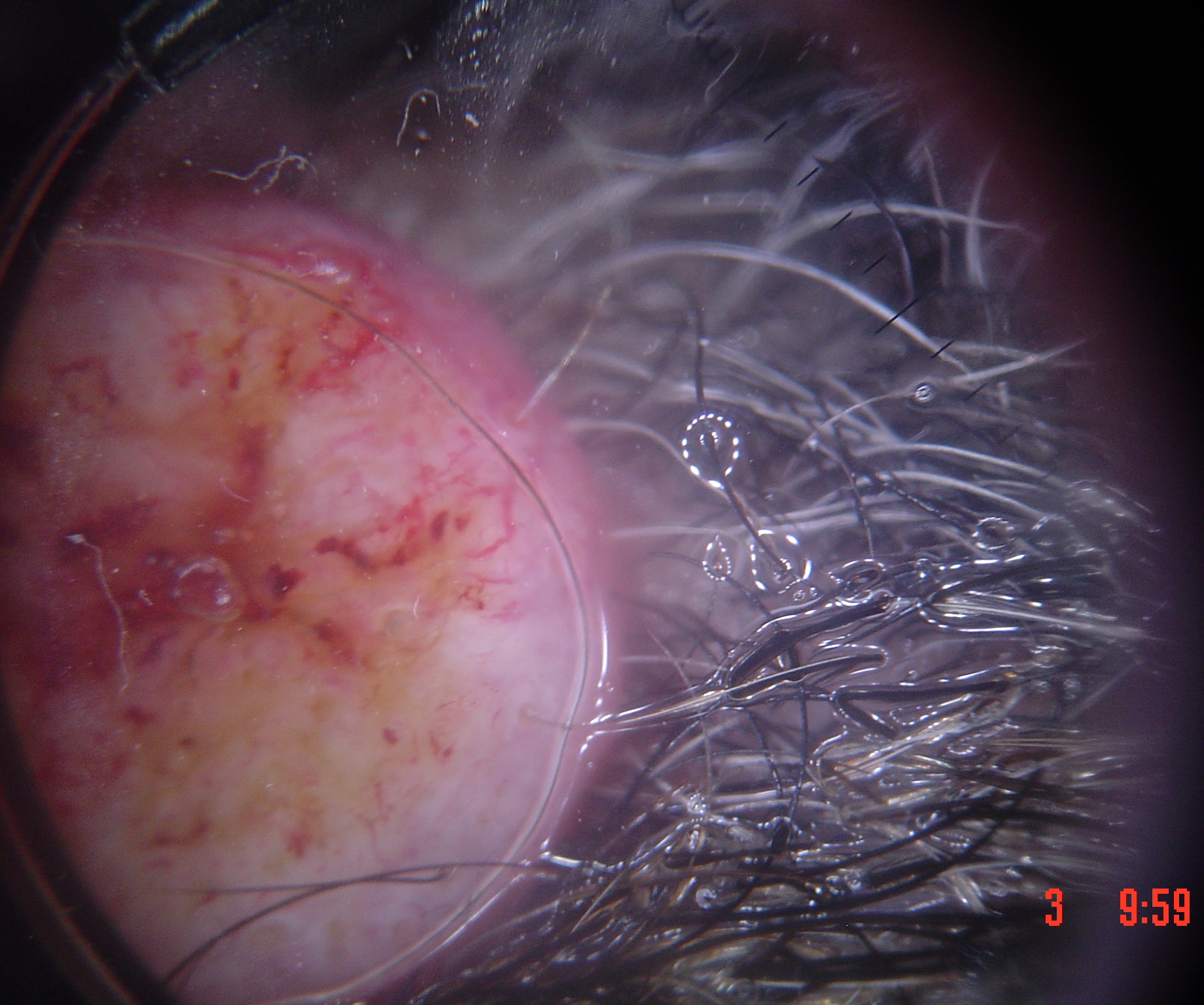Case:
Dermoscopy of a skin lesion.
Diagnosis:
Histopathologically confirmed as a malignant, keratinocytic lesion — a squamous cell carcinoma.